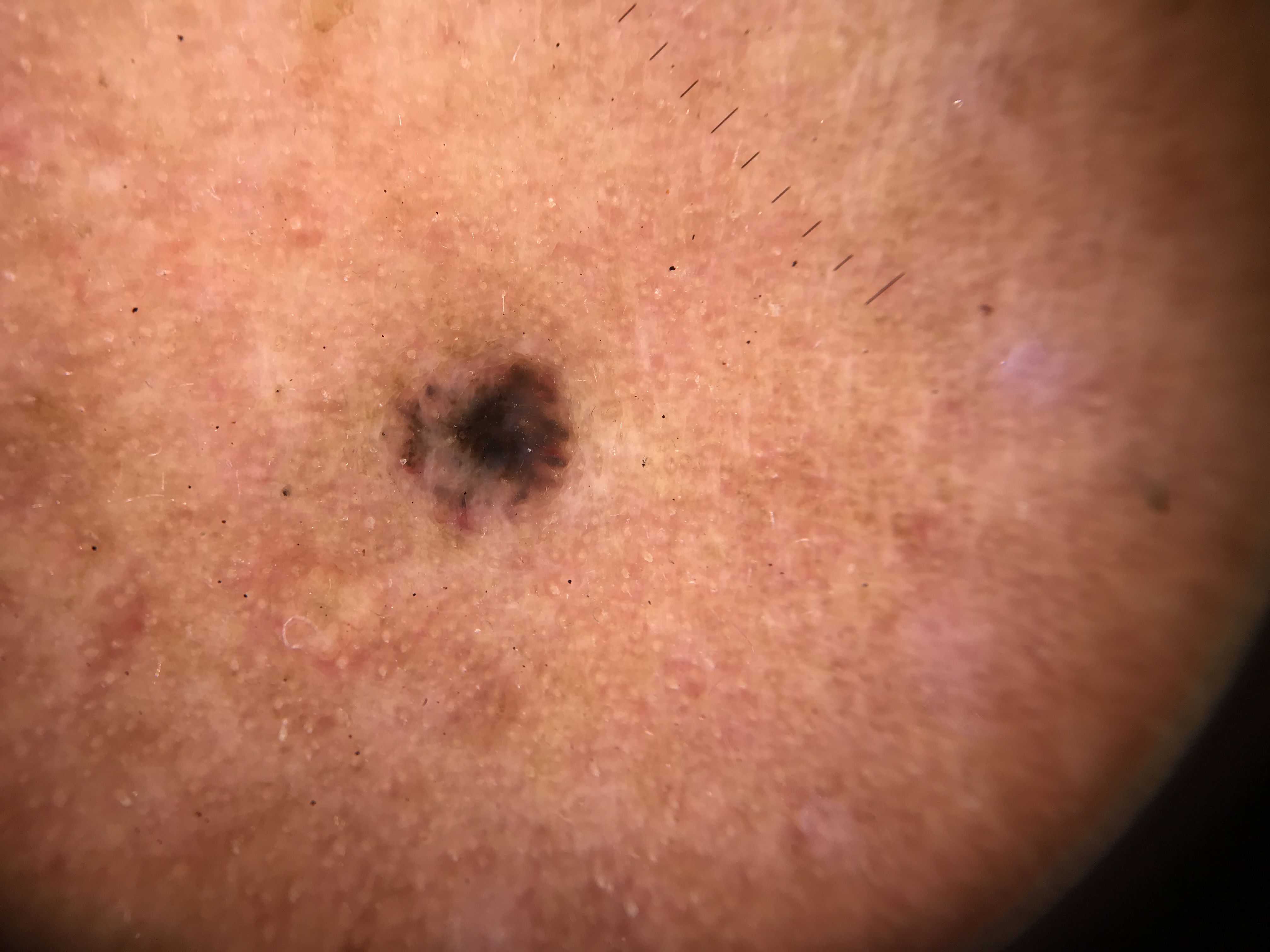label: basal cell carcinoma (biopsy-proven)